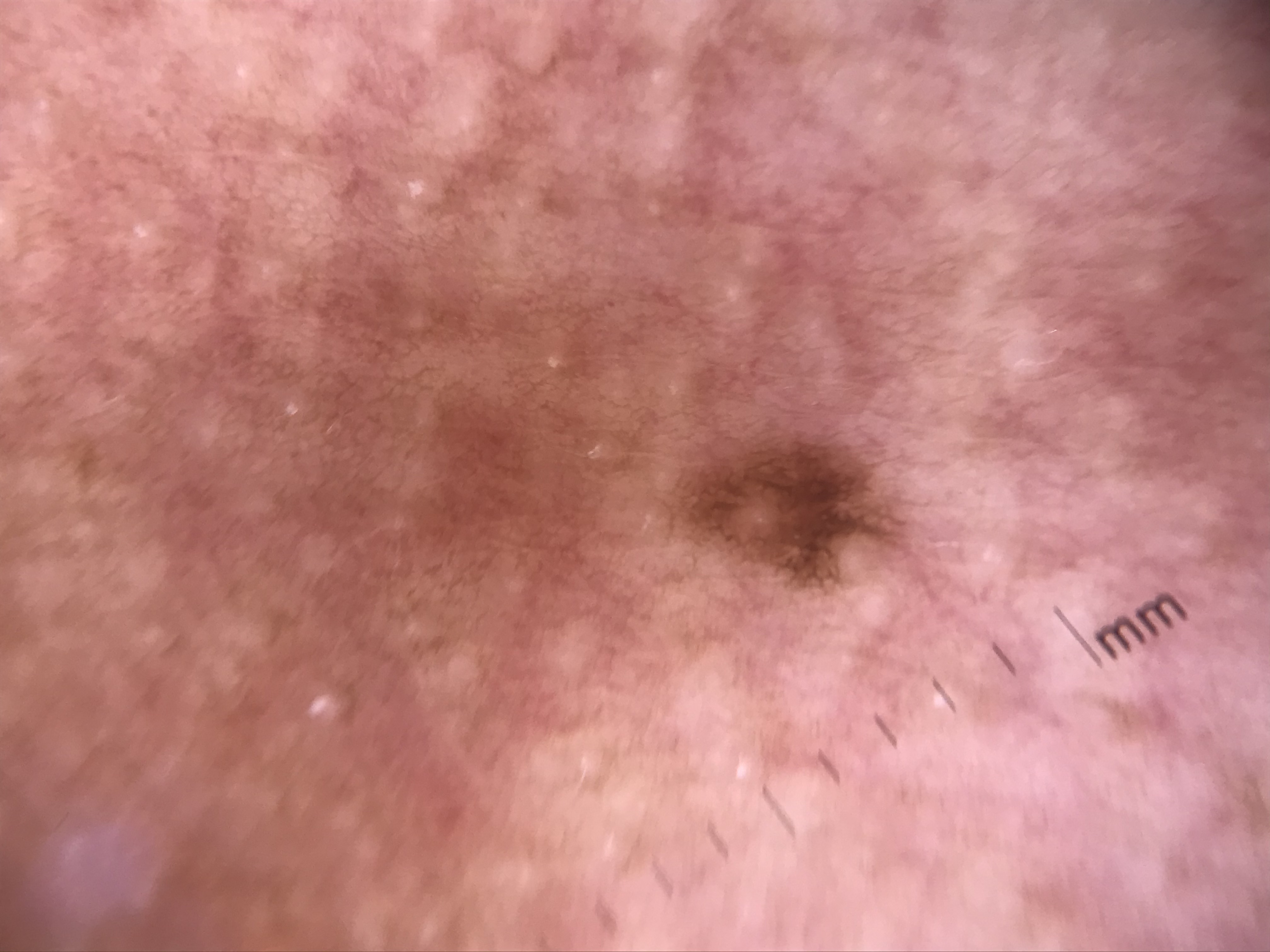{
  "image": "dermoscopy",
  "diagnosis": {
    "name": "junctional nevus",
    "code": "jb",
    "malignancy": "benign",
    "super_class": "melanocytic",
    "confirmation": "expert consensus"
  }
}